A dermoscopic close-up of a skin lesion:
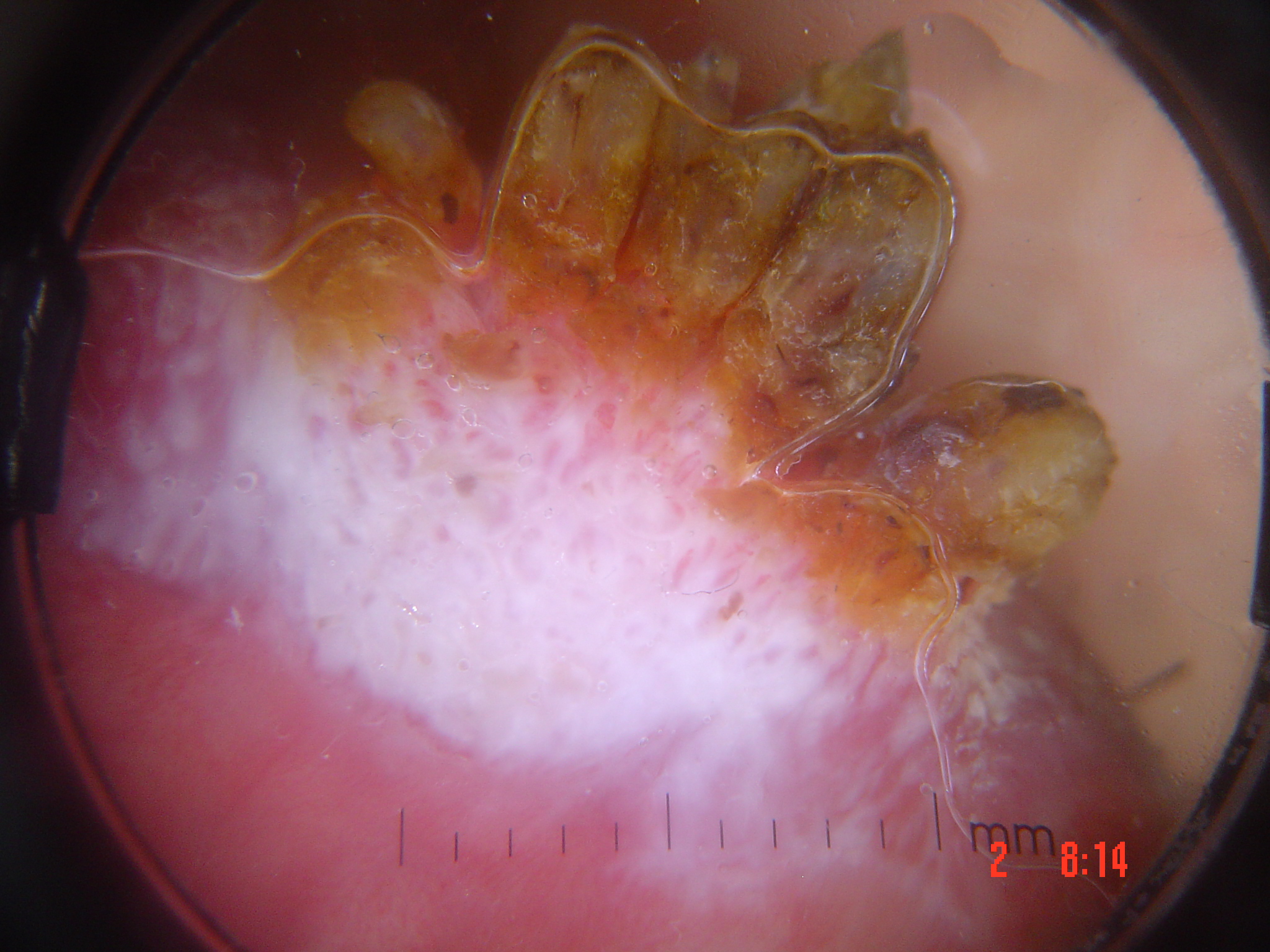The morphology is that of a keratinocytic lesion.
The biopsy diagnosis was a malignancy — a squamous cell carcinoma.